A dermatoscopic image of a skin lesion.
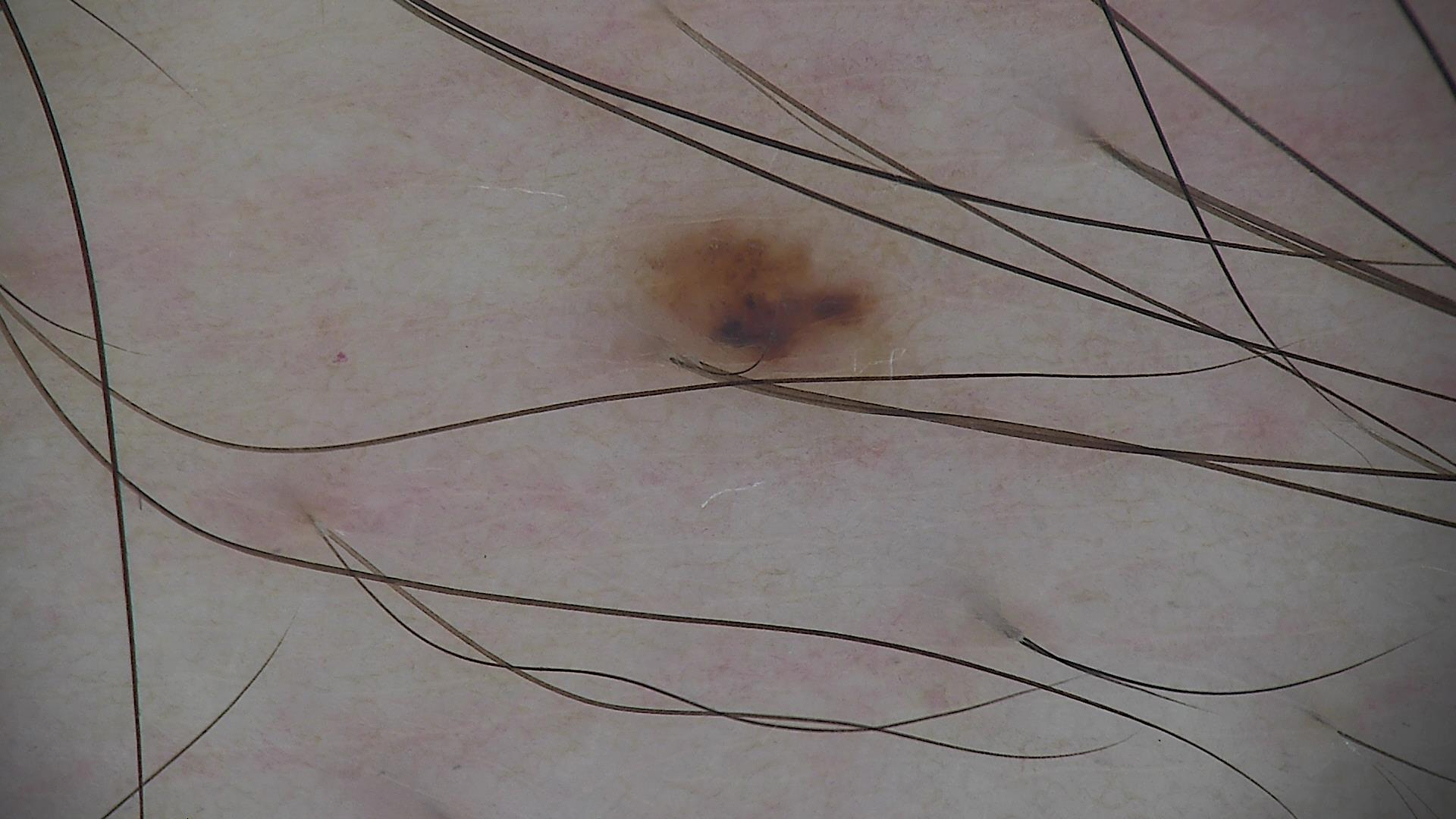assessment — dysplastic junctional nevus (expert consensus)